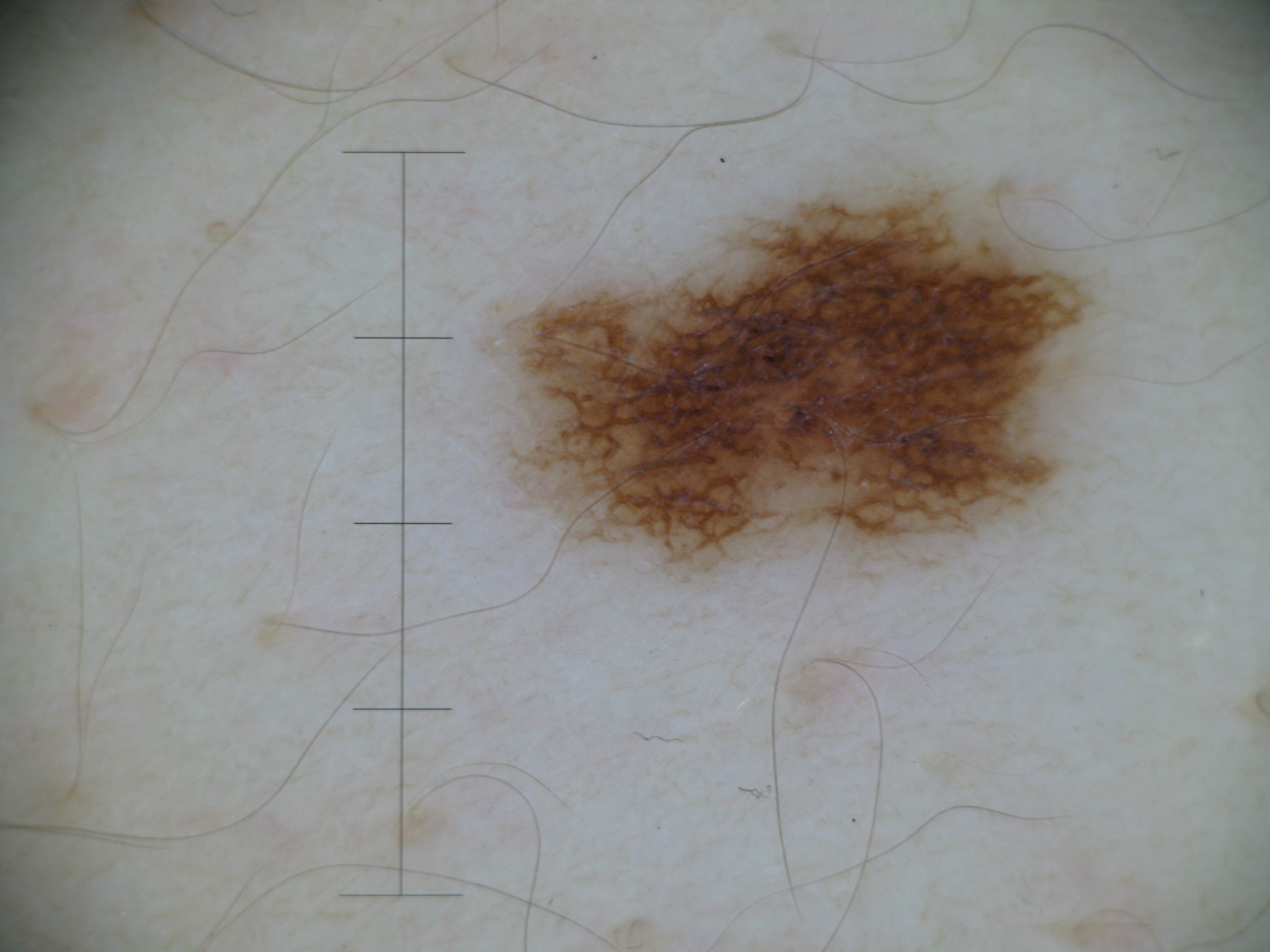A dermoscopic image of a skin lesion. This is a banal lesion. The diagnostic label was a junctional nevus.